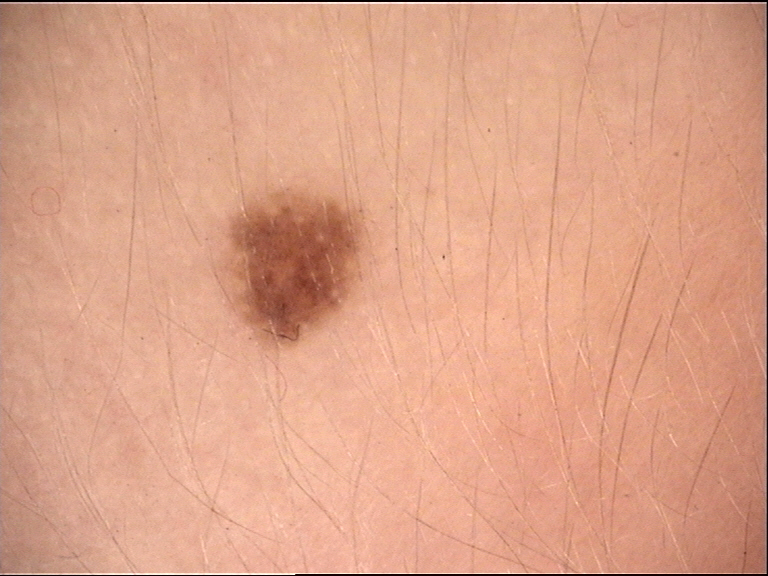A dermoscopic image of a skin lesion. The diagnostic label was a banal lesion — a junctional nevus.